The photograph was taken at an angle.
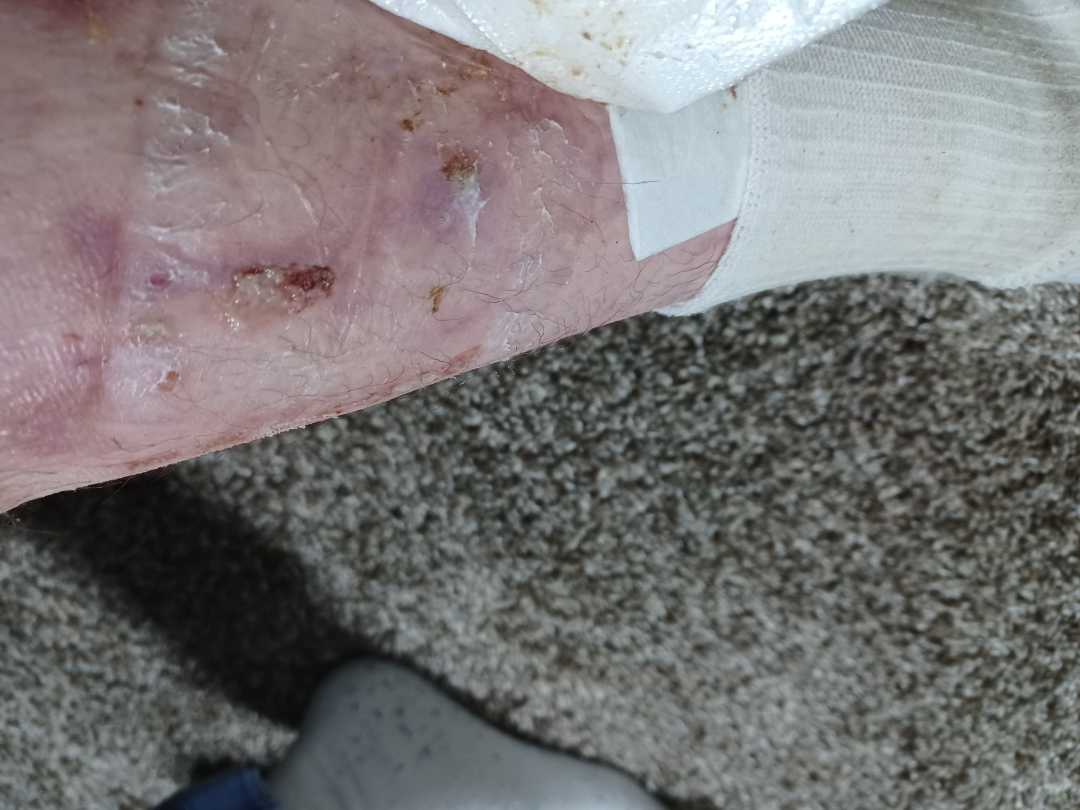The skin findings could not be characterized from the image. FST II.